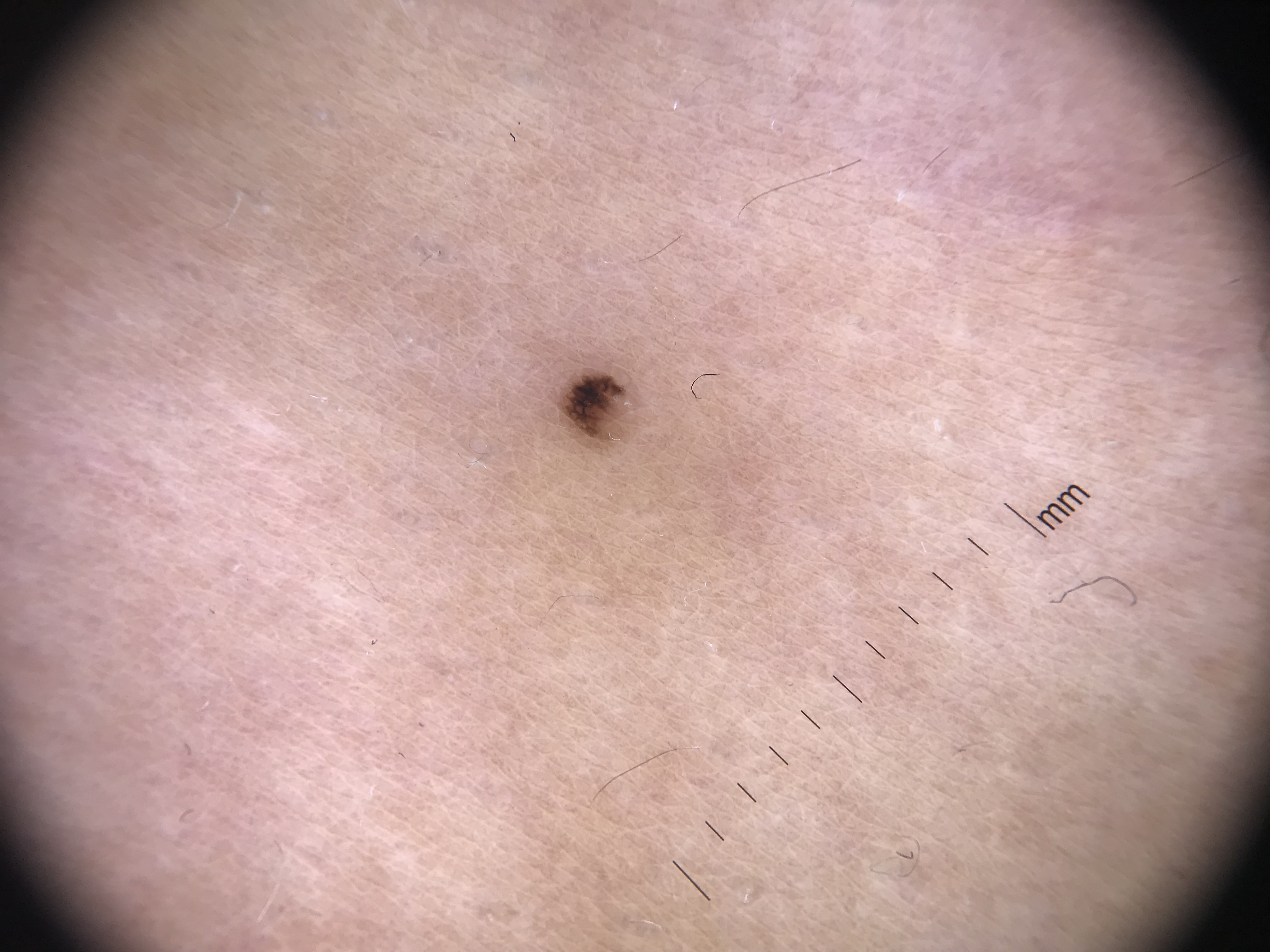Dermoscopy of a skin lesion.
The diagnostic label was a banal lesion — a junctional nevus.